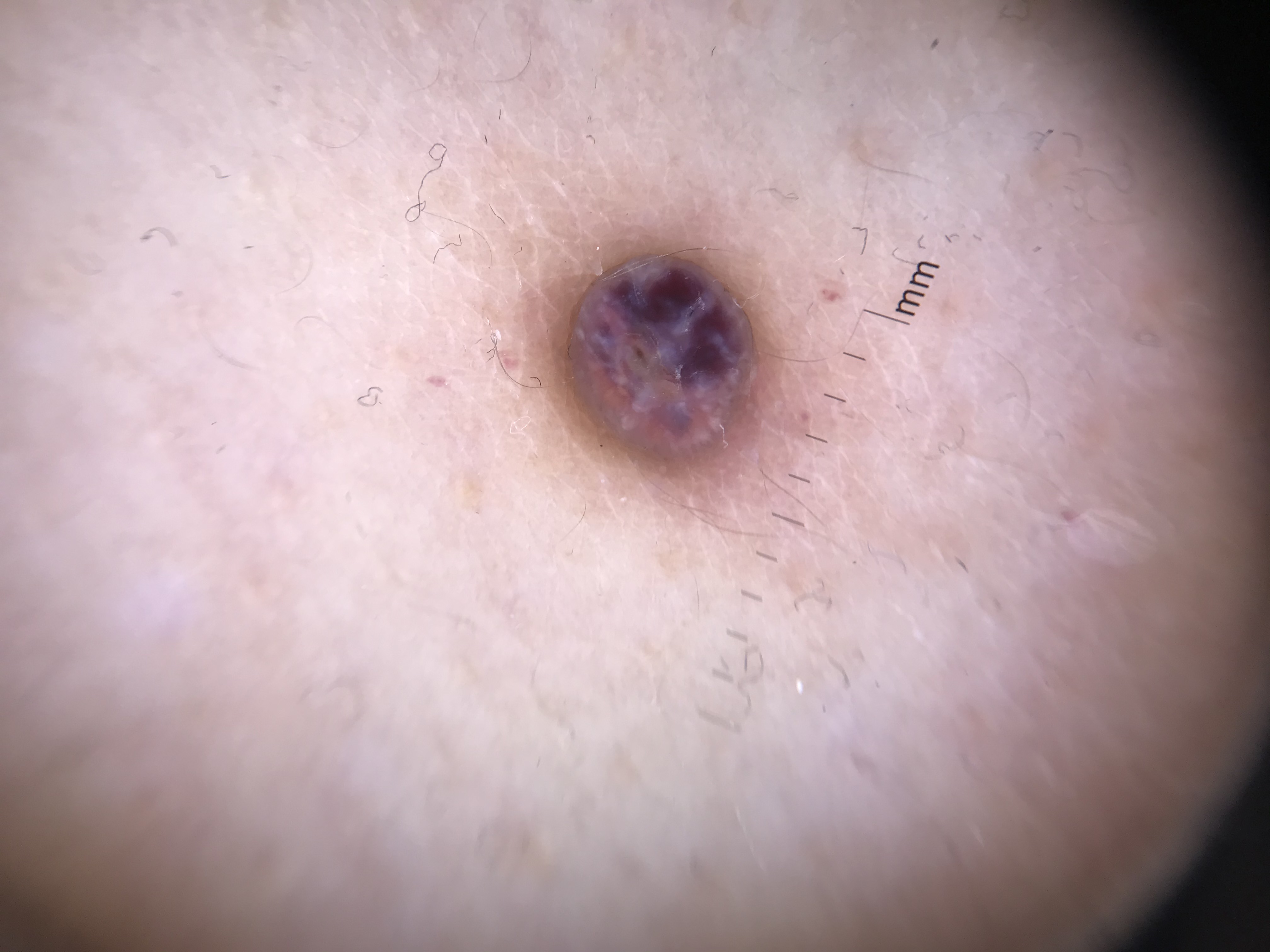Q: What is the diagnosis?
A: Kaposi sarcoma (biopsy-proven)